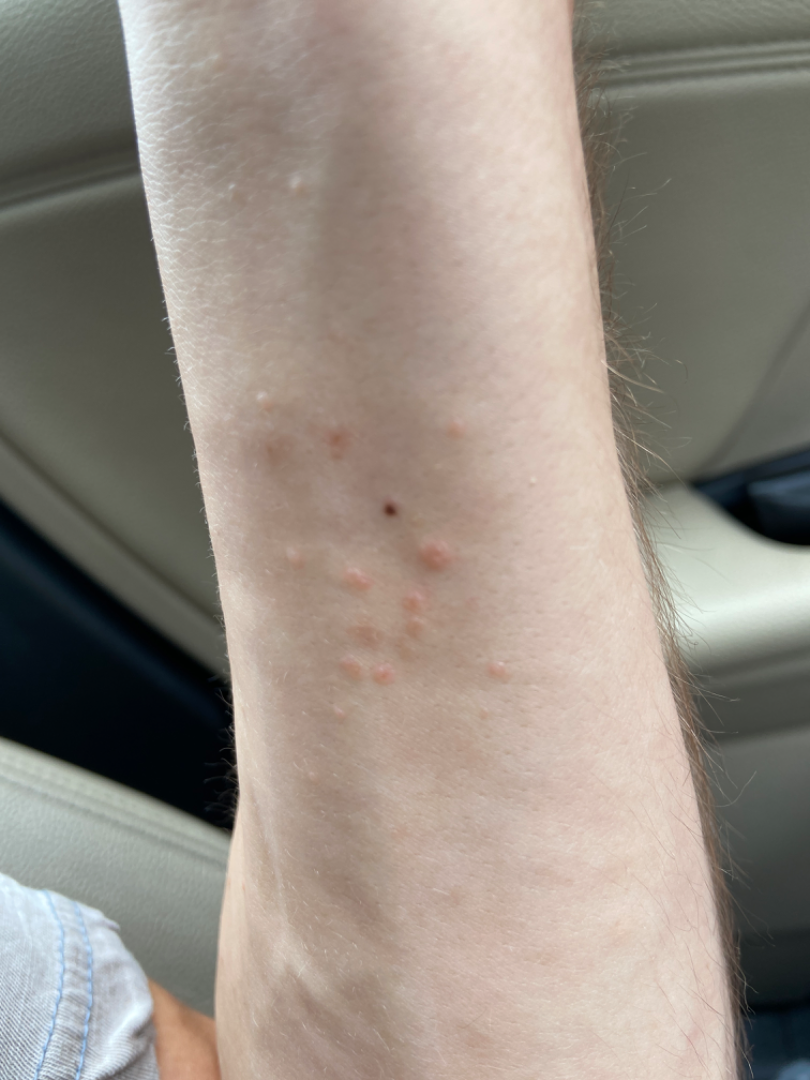The photo was captured at an angle. The palm, arm and back of the hand are involved. On photographic review by a dermatologist, Granuloma annulare (possible); Insect Bite (possible); Allergic Contact Dermatitis (possible).